Located on the leg. The photograph is a close-up of the affected area — 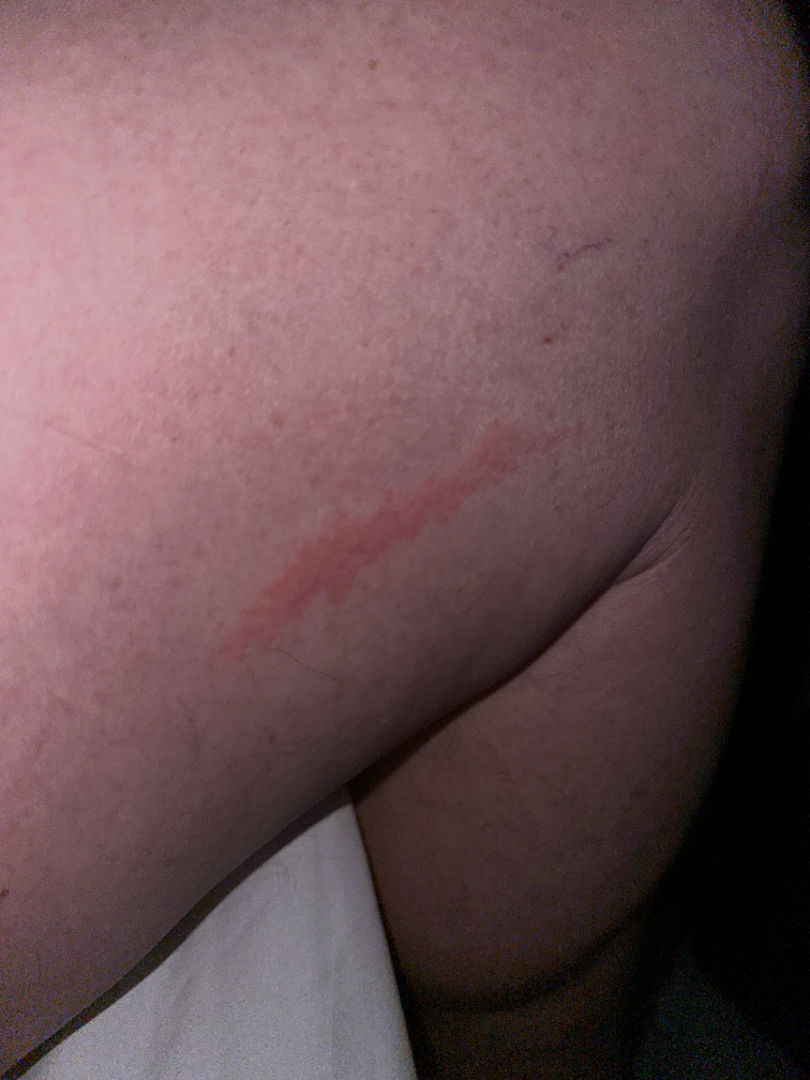Urticaria and Allergic Contact Dermatitis were considered with similar weight.